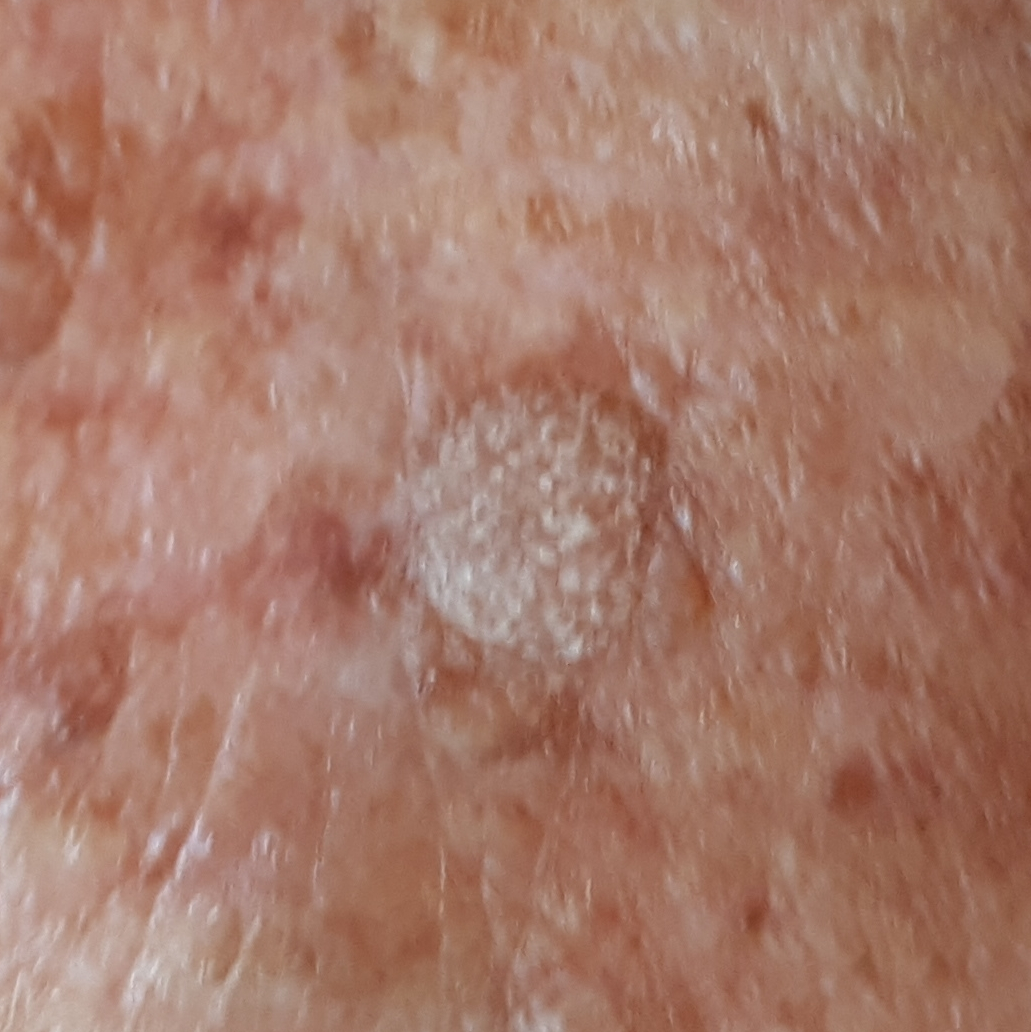A patient in their 80s.
A clinical photograph of a skin lesion.
The lesion is on the chest.
The patient reports that the lesion is elevated and has grown.
Clinically diagnosed as a seborrheic keratosis.